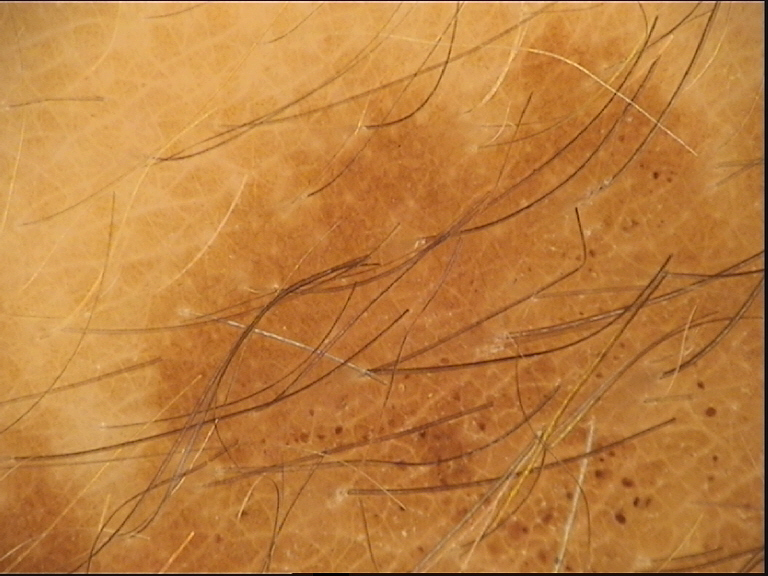{
  "image": "dermatoscopy",
  "lesion_type": {
    "main_class": "banal",
    "pattern": "compound"
  },
  "diagnosis": {
    "name": "congenital compound nevus",
    "code": "ccb",
    "malignancy": "benign",
    "super_class": "melanocytic",
    "confirmation": "expert consensus"
  }
}